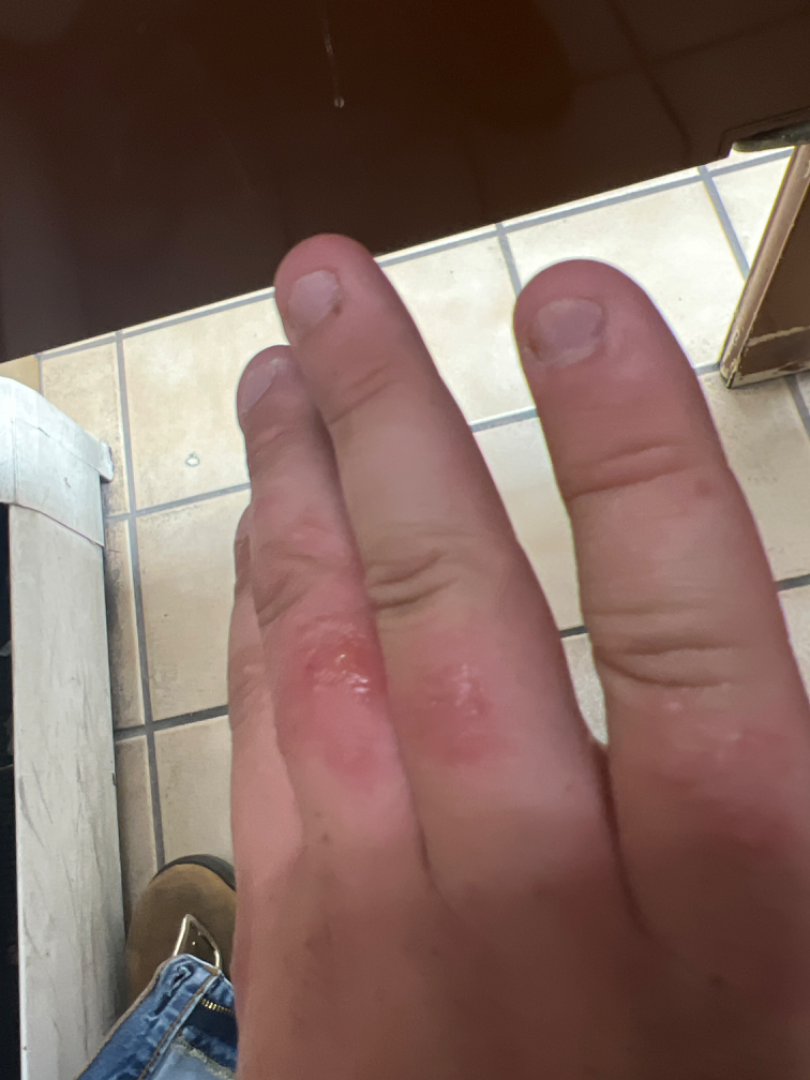Present for less than one week.
The patient indicates bothersome appearance and itching.
The lesion is described as fluid-filled and raised or bumpy.
An image taken at an angle.
The patient is a male aged 18–29.
No associated systemic symptoms reported.
The affected area is the back of the hand.
Burn of skin (considered); Allergic Contact Dermatitis (considered); Impetigo (unlikely).